This is a close-up image; the arm and leg are involved: 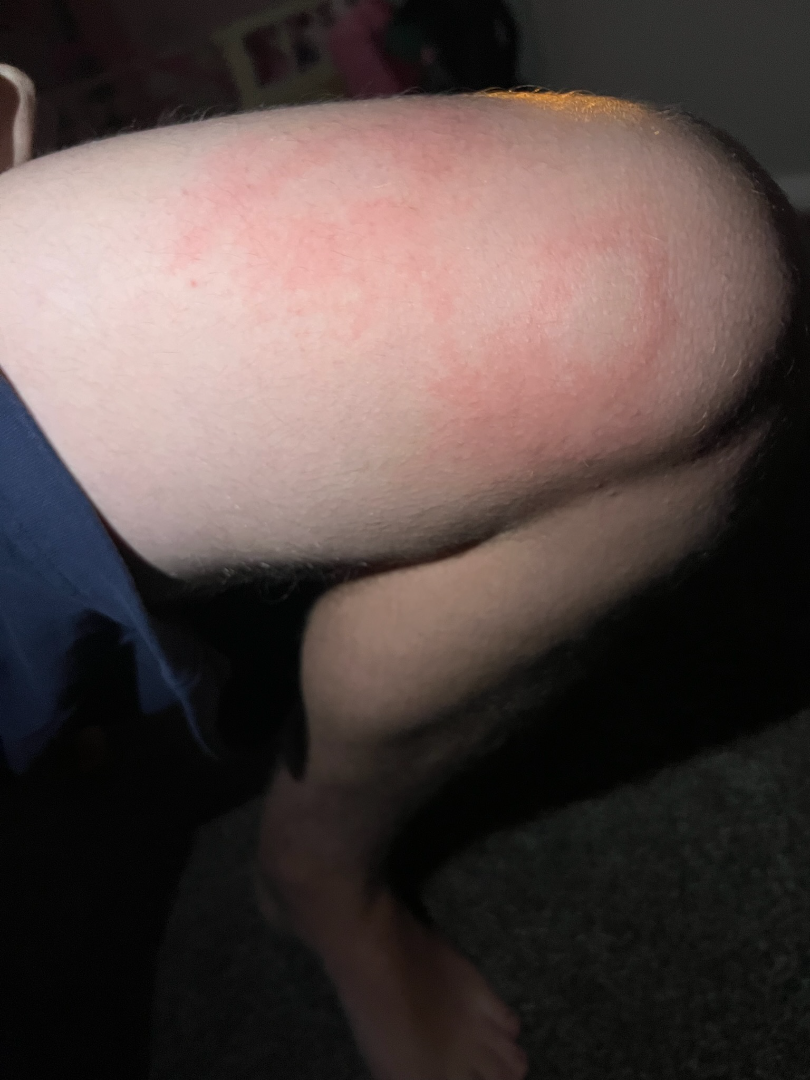Texture is reported as raised or bumpy. No associated systemic symptoms reported. Reported duration is about one day. Symptoms reported: itching, enlargement and bothersome appearance. Self-categorized by the patient as a rash. The reviewing clinician's impression was: consistent with Urticaria.